A dermoscopy image of a single skin lesion.
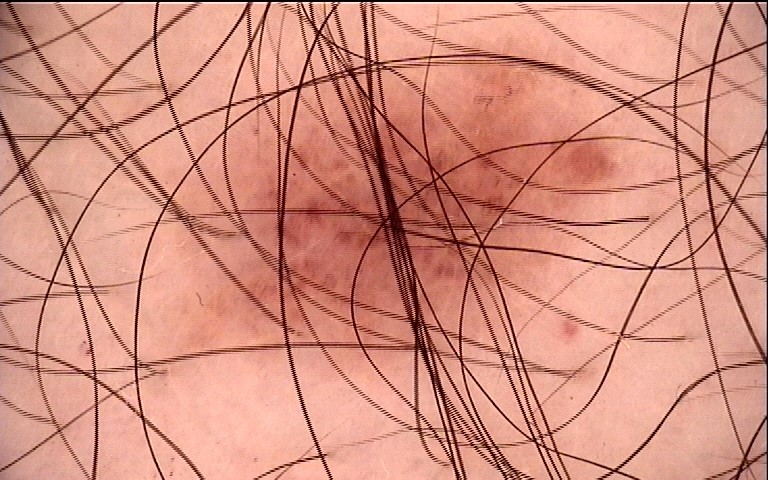| key | value |
|---|---|
| diagnosis | dysplastic junctional nevus (expert consensus) |